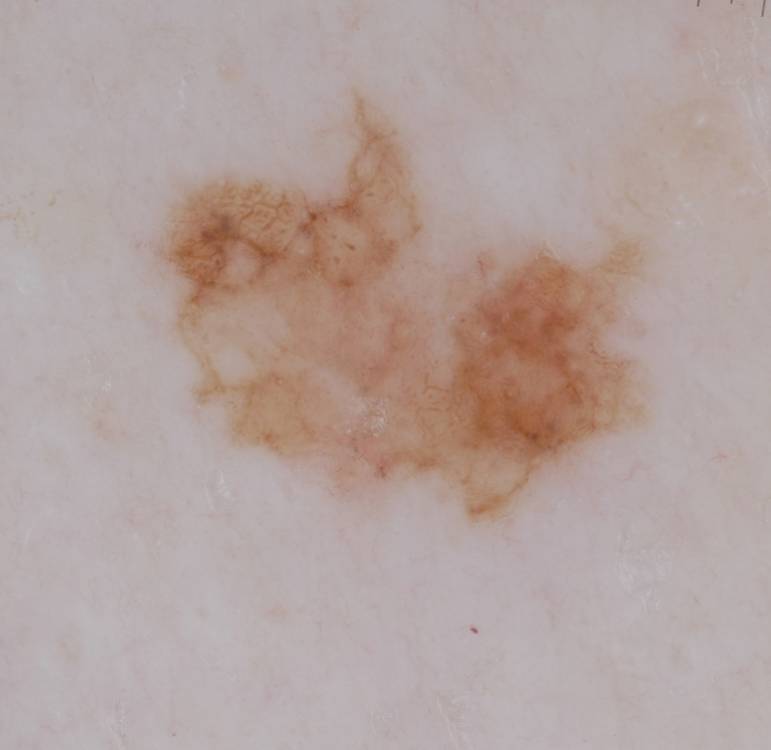Case summary:
- image type · dermoscopic image
- dermoscopic findings · globules and pigment network; absent: milia-like cysts, streaks, and negative network
- lesion location · 151, 86, 652, 523
- lesion size · ~22% of the field
- diagnostic label · a melanoma